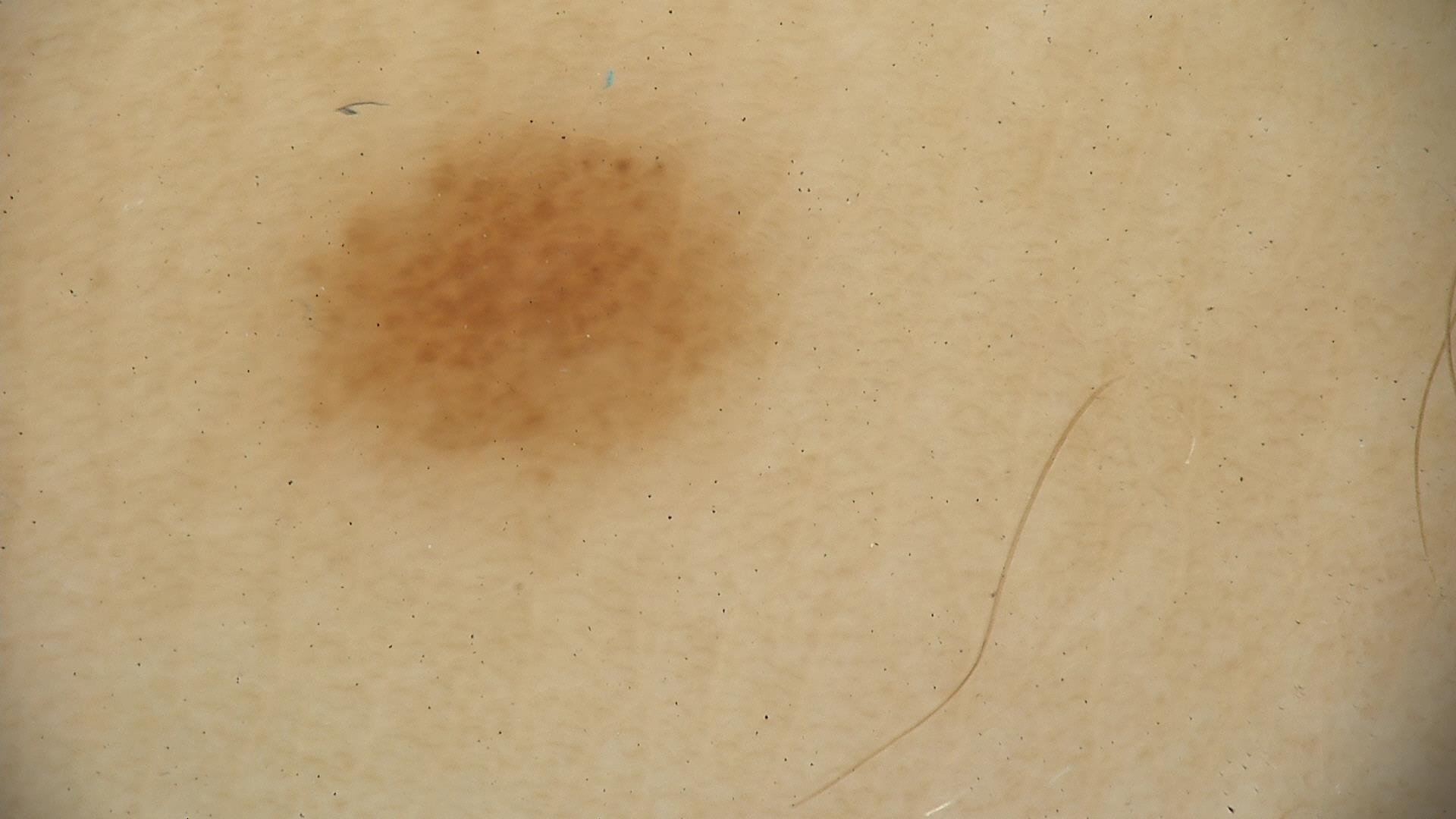modality = dermoscopy
diagnostic label = dysplastic junctional nevus (expert consensus)